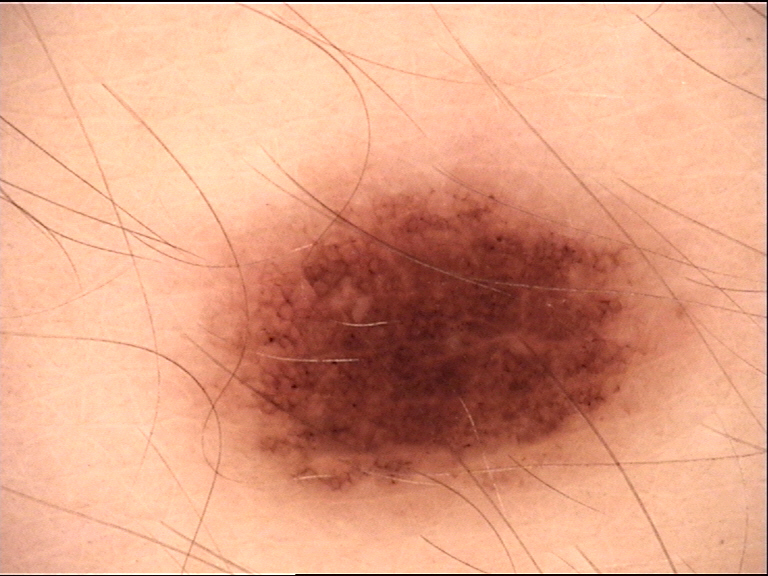A dermoscopic photograph of a skin lesion. Labeled as a benign lesion — a dysplastic junctional nevus.